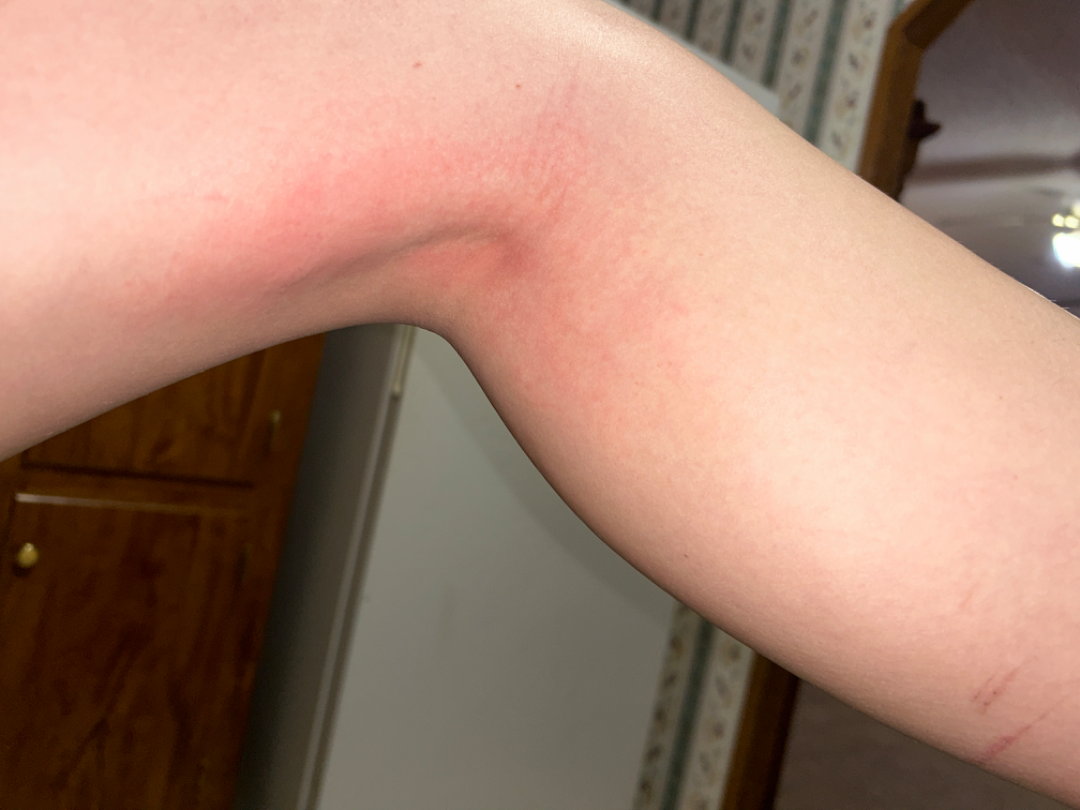Located on the leg. The lesion is described as raised or bumpy. Lay reviewers estimated Monk skin tone scale 2 or 3. The photo was captured at a distance. The patient reports the condition has been present for less than one week. The reviewing clinician's impression was: Allergic Contact Dermatitis and Irritant Contact Dermatitis were considered with similar weight.